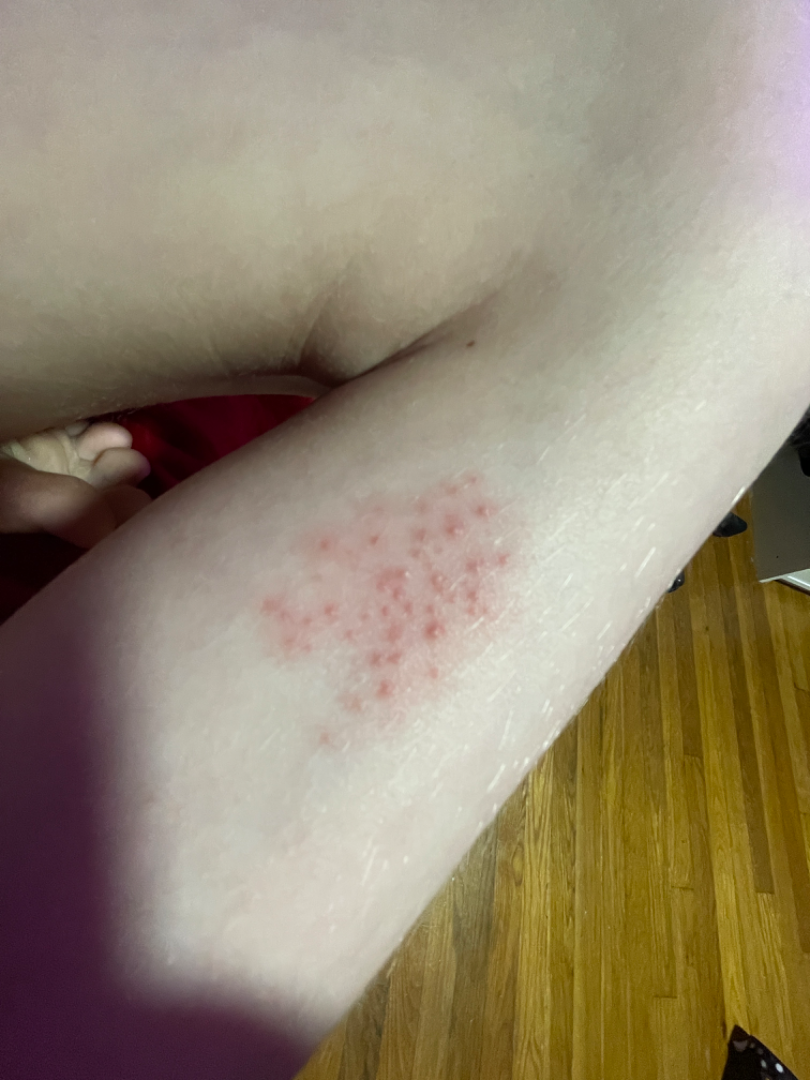{
  "differential": {
    "tied_lead": [
      "Folliculitis",
      "Allergic Contact Dermatitis",
      "Herpes Simplex"
    ]
  }
}